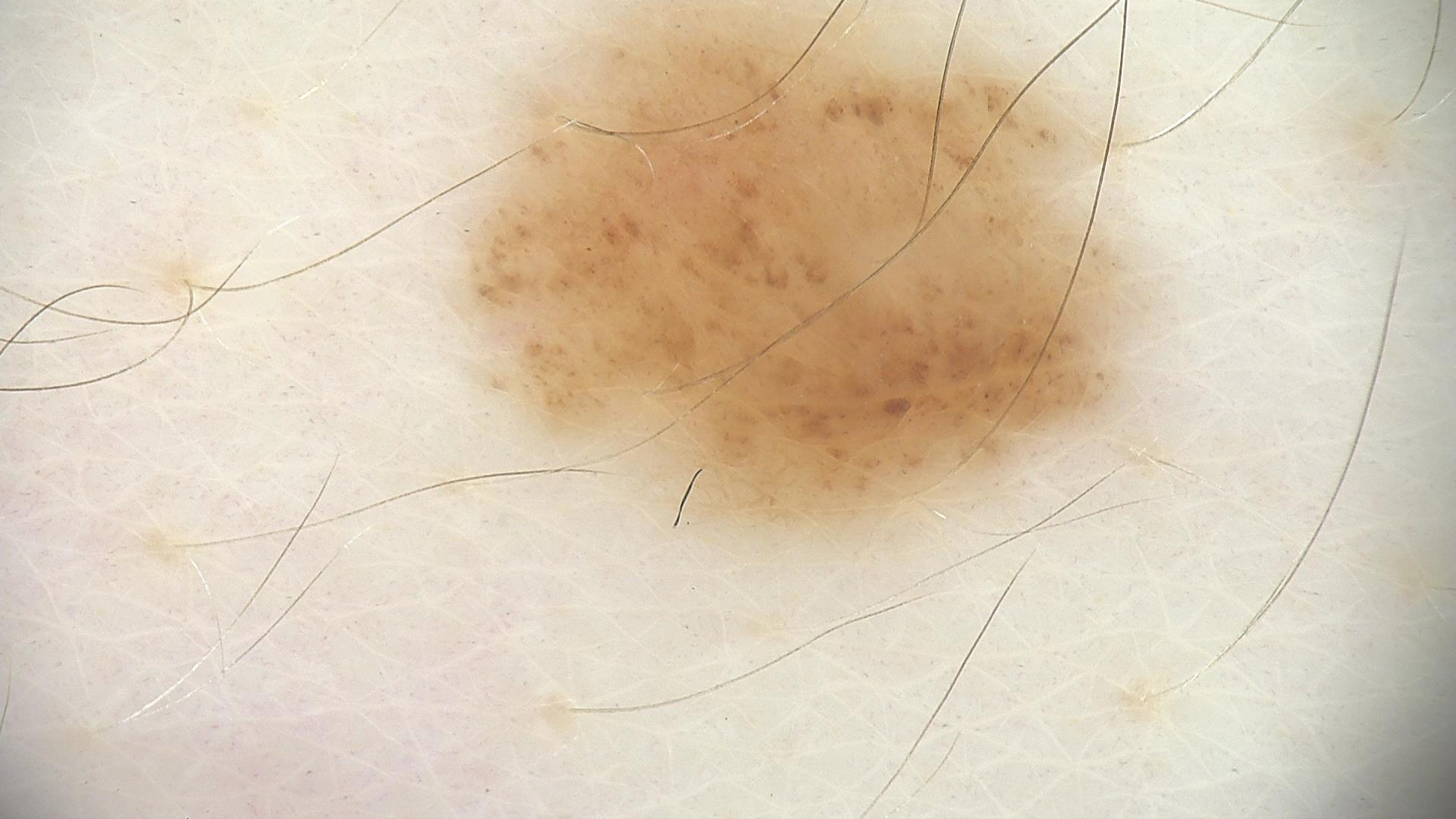A dermatoscopic image of a skin lesion.
The diagnostic label was a dysplastic junctional nevus.